A skin lesion imaged with a dermatoscope: 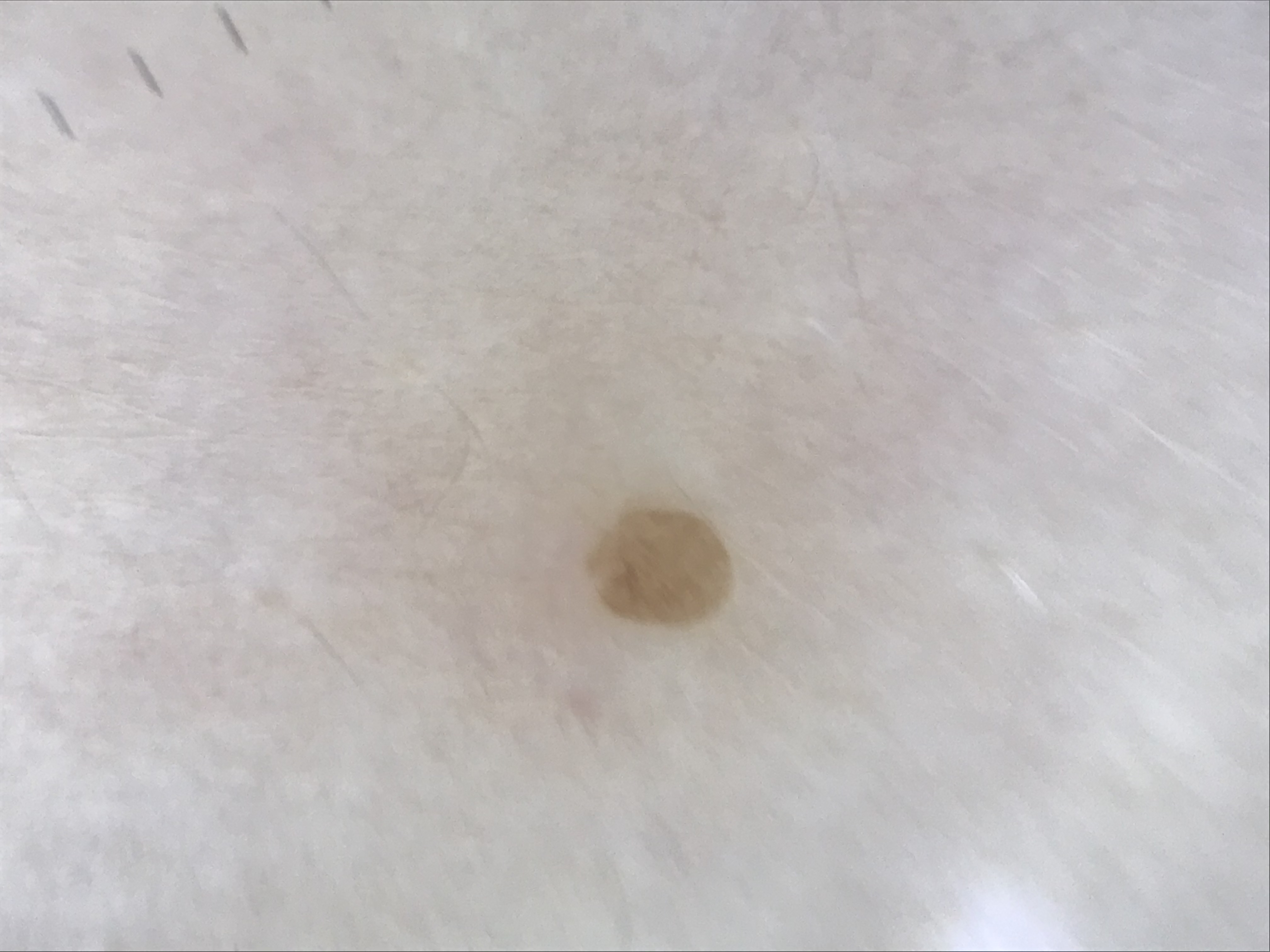The architecture is that of a keratinocytic lesion.
Classified as a seborrheic keratosis.